Dermoscopy of a skin lesion.
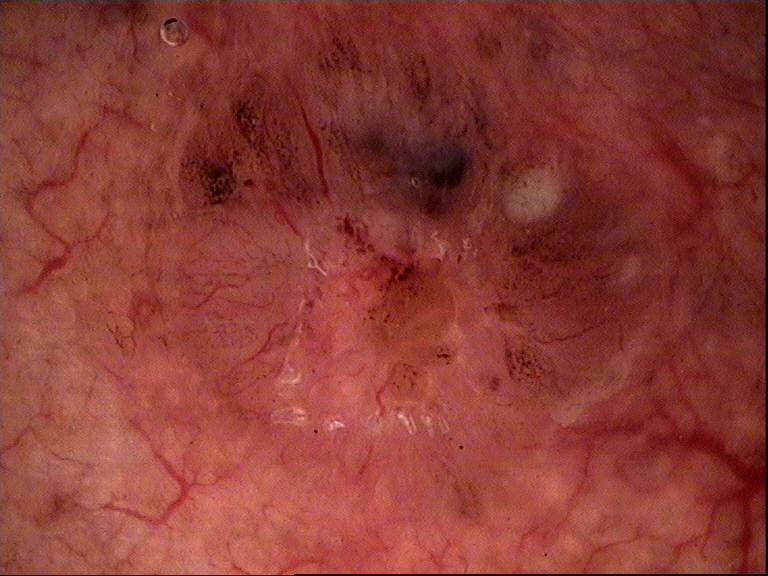Q: What is this lesion?
A: basal cell carcinoma (biopsy-proven)